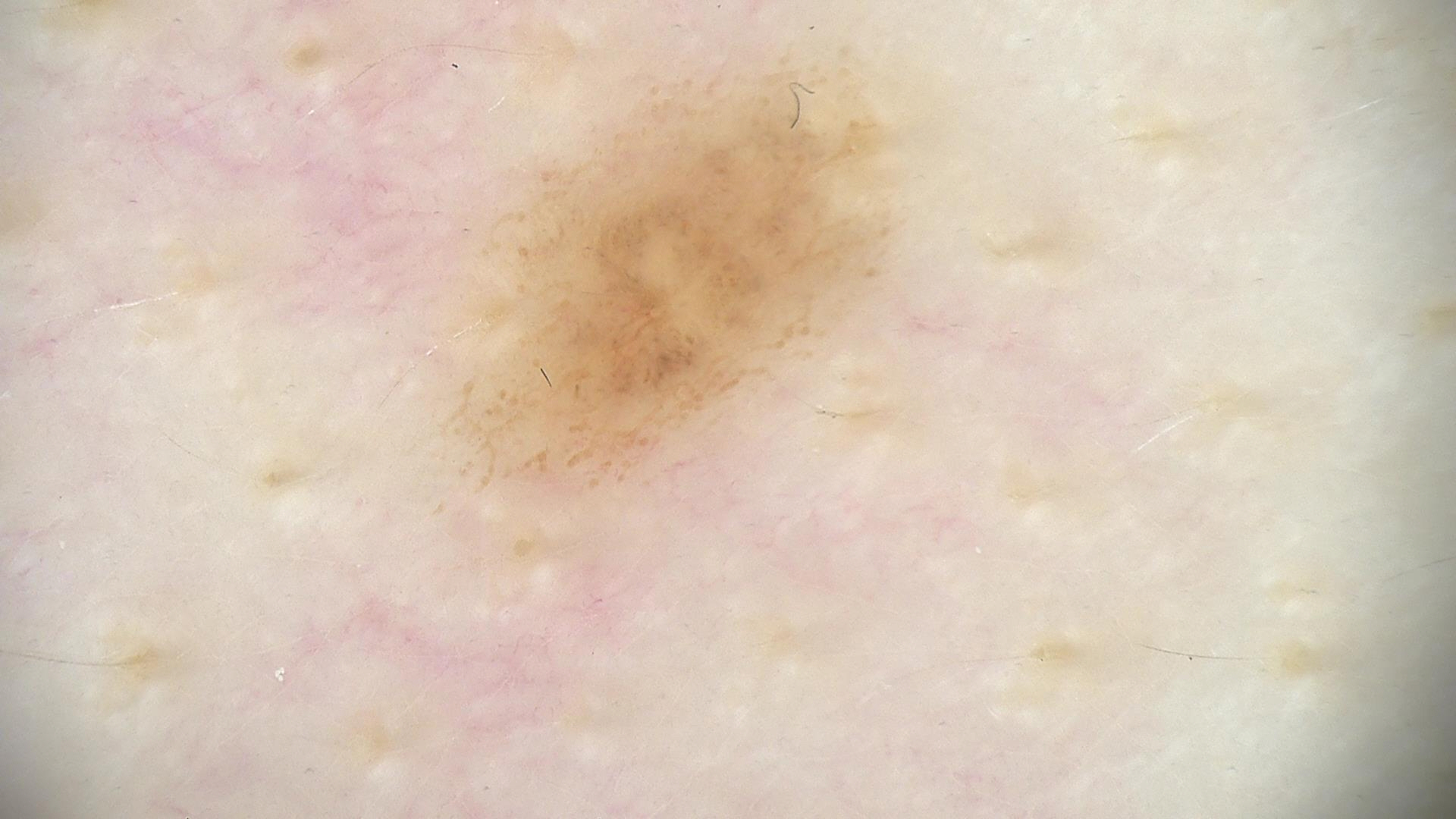assessment: dysplastic junctional nevus (expert consensus).